A skin lesion imaged with a dermatoscope:
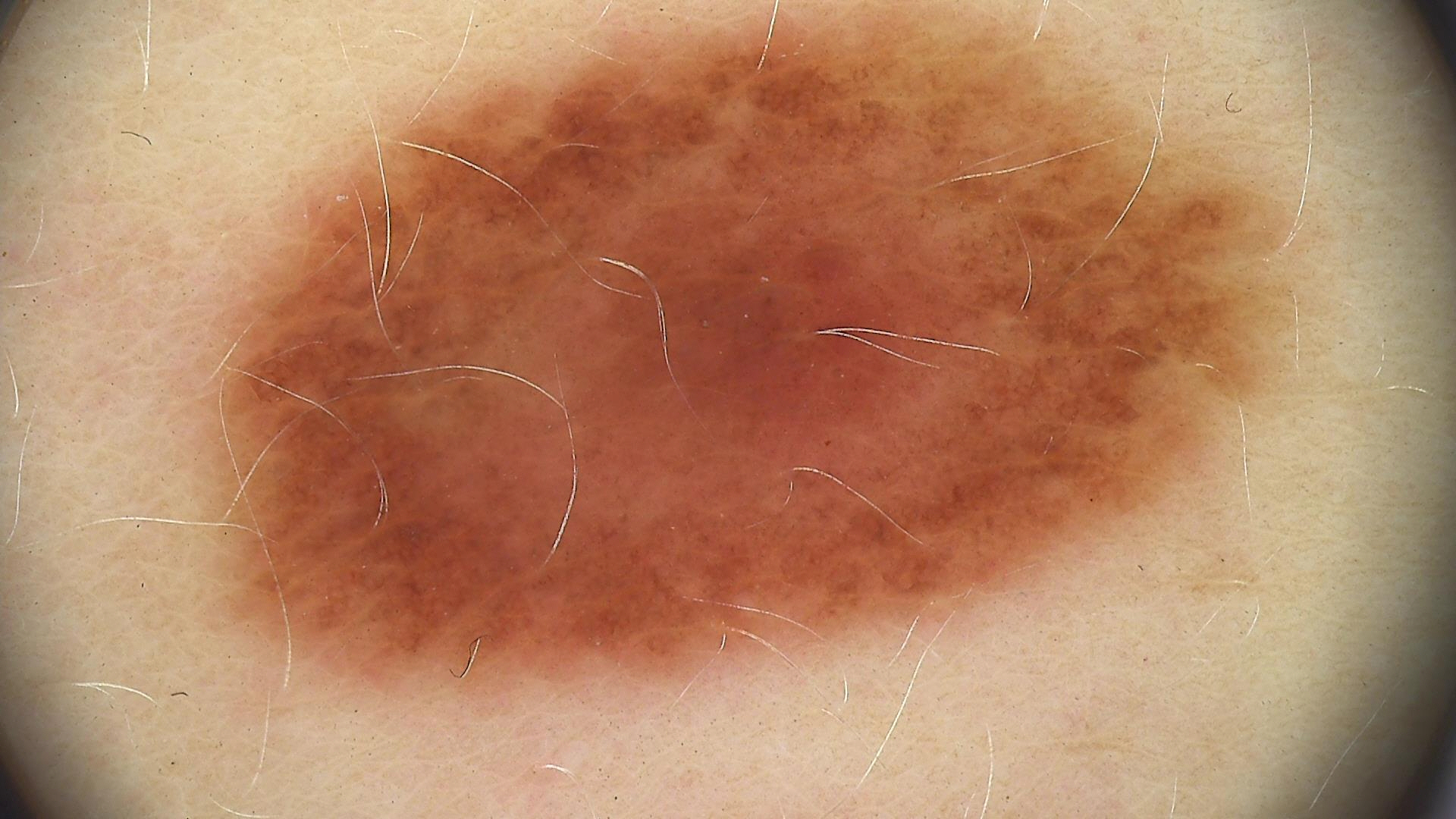{"diagnosis": {"name": "dysplastic junctional nevus", "code": "jd", "malignancy": "benign", "super_class": "melanocytic", "confirmation": "expert consensus"}}